A dermatoscopic image of a skin lesion:
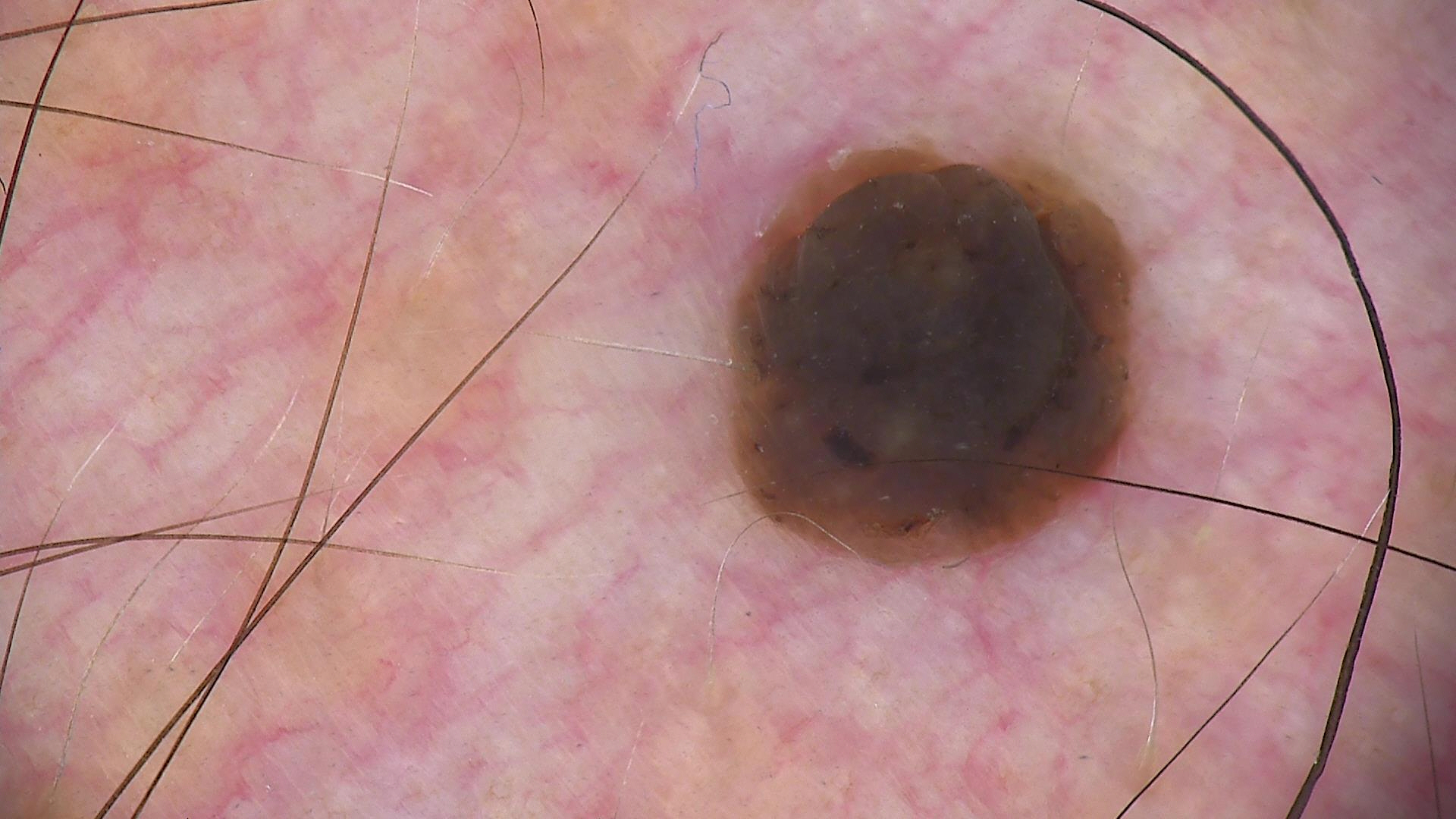assessment — seborrheic keratosis (expert consensus).